The lesion involves the leg, a close-up photograph, the patient is female.
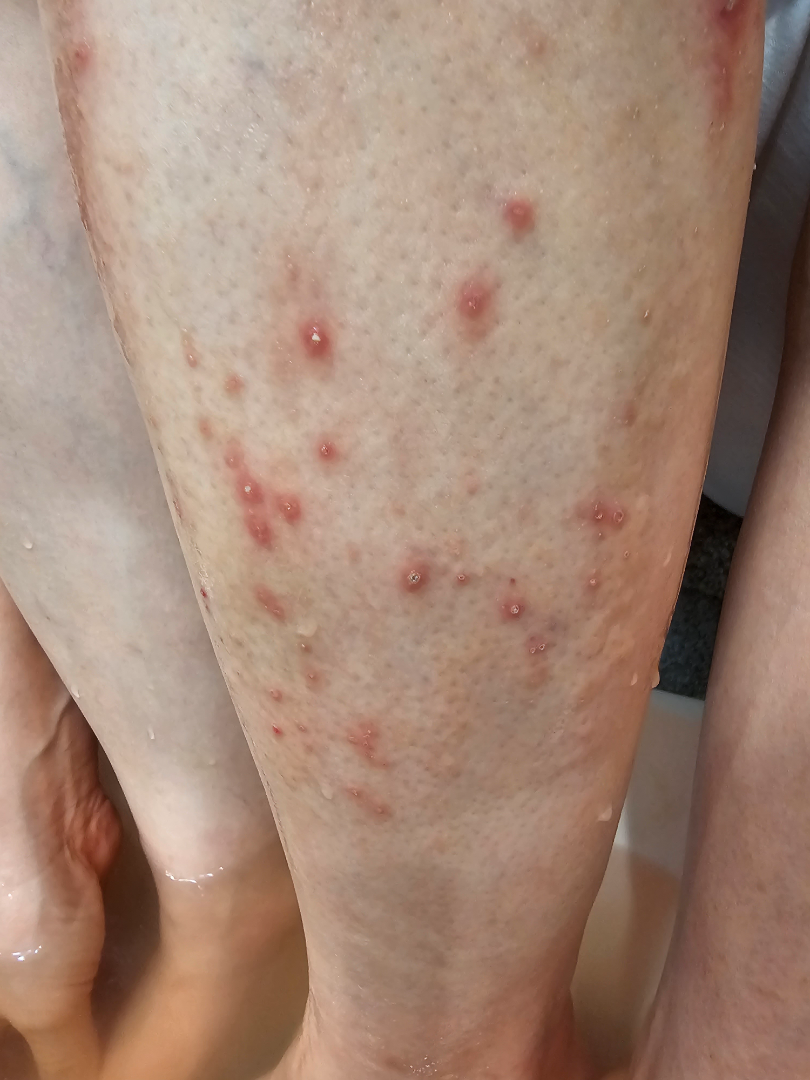Findings:
– dermatologist impression · single-reviewer assessment: the differential is split between Perforating dermatosis and Psoriasis